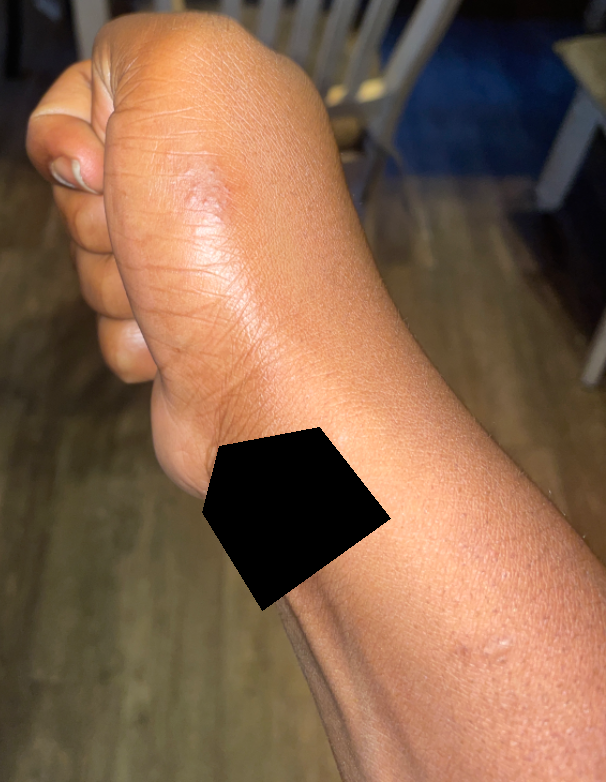Assessment:
The case was indeterminate on photographic review.